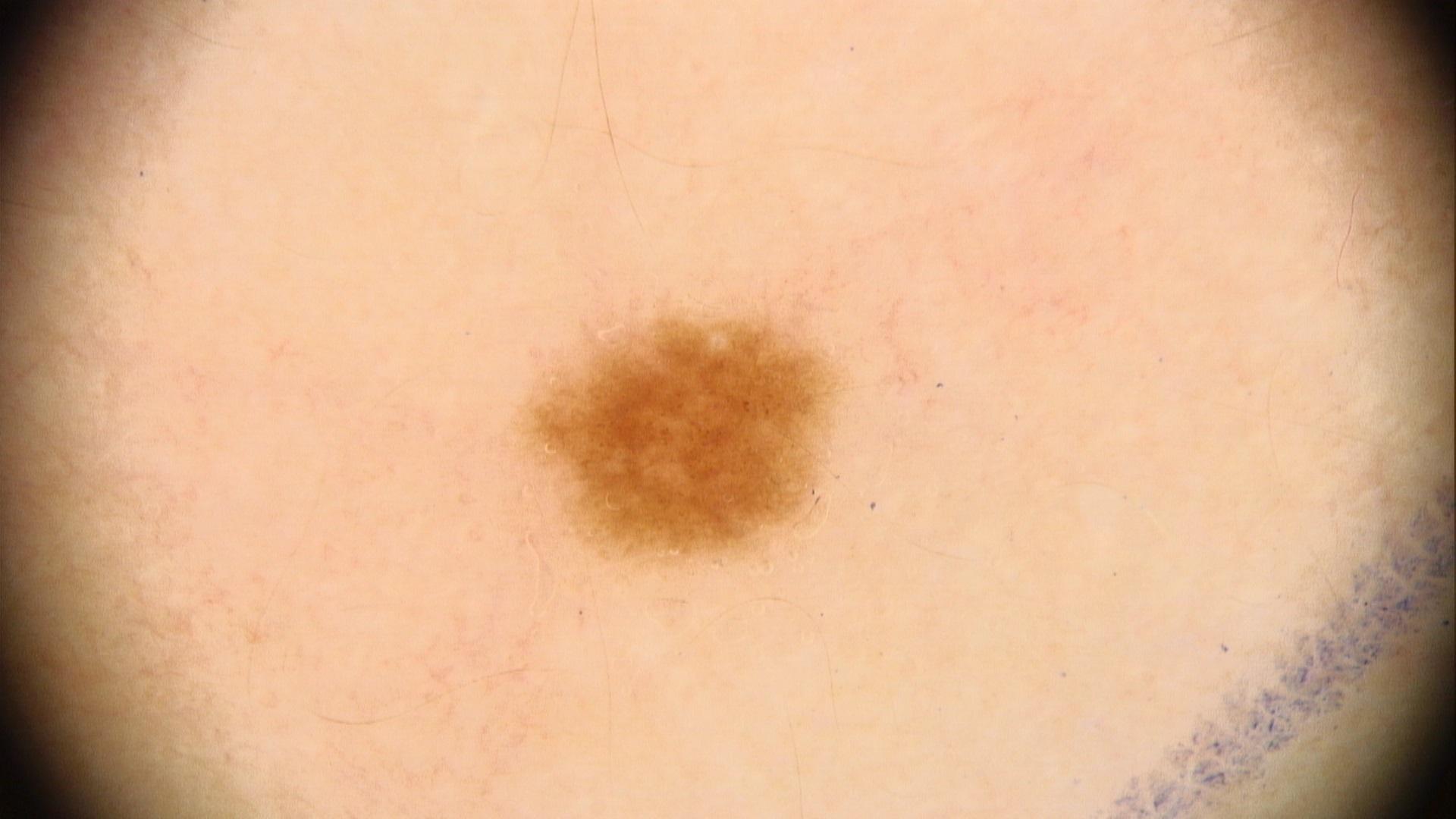Case summary: Located on the trunk. Impression: Expert review favored a benign lesion — a nevus.